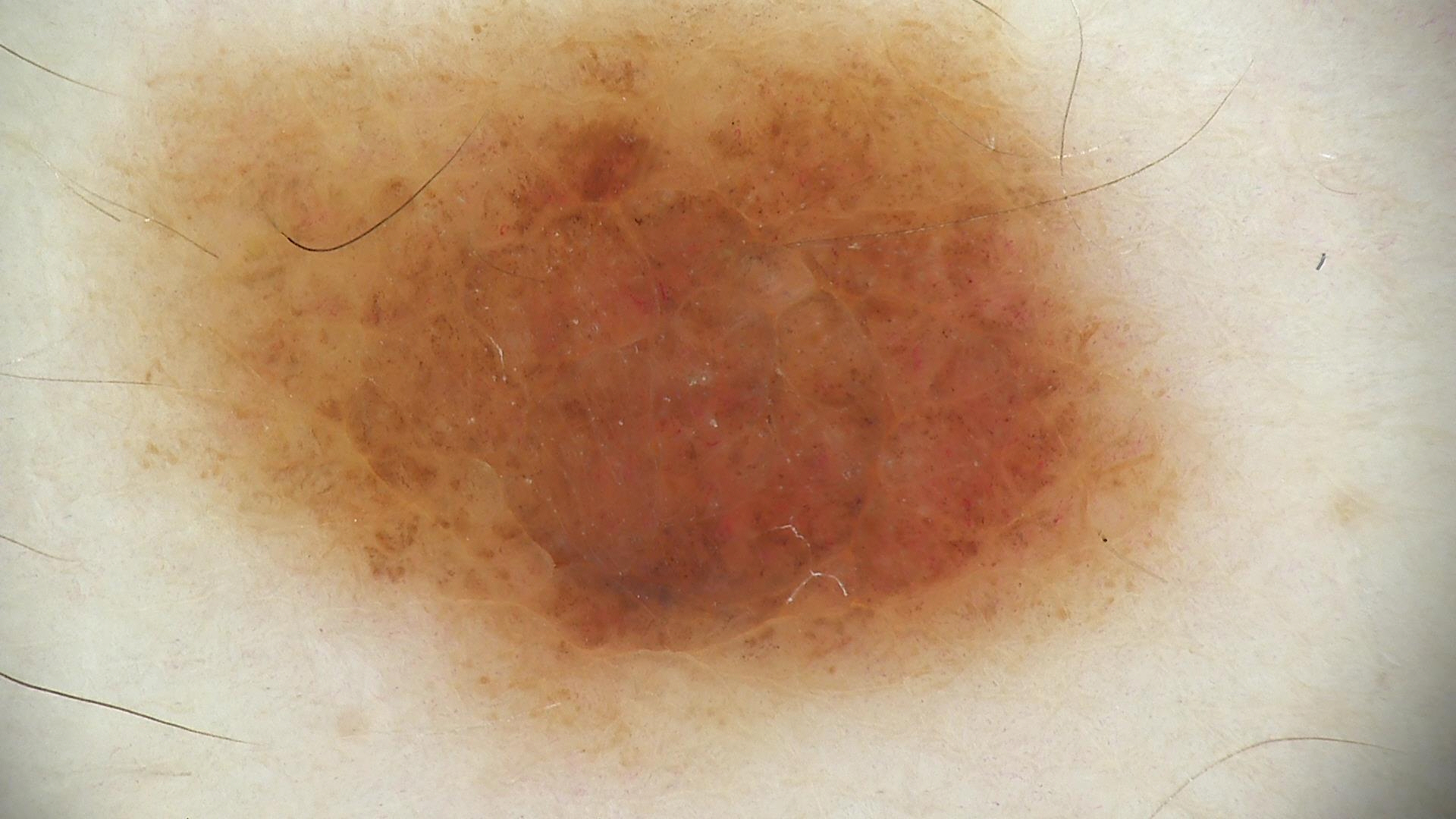Classified as a compound nevus.